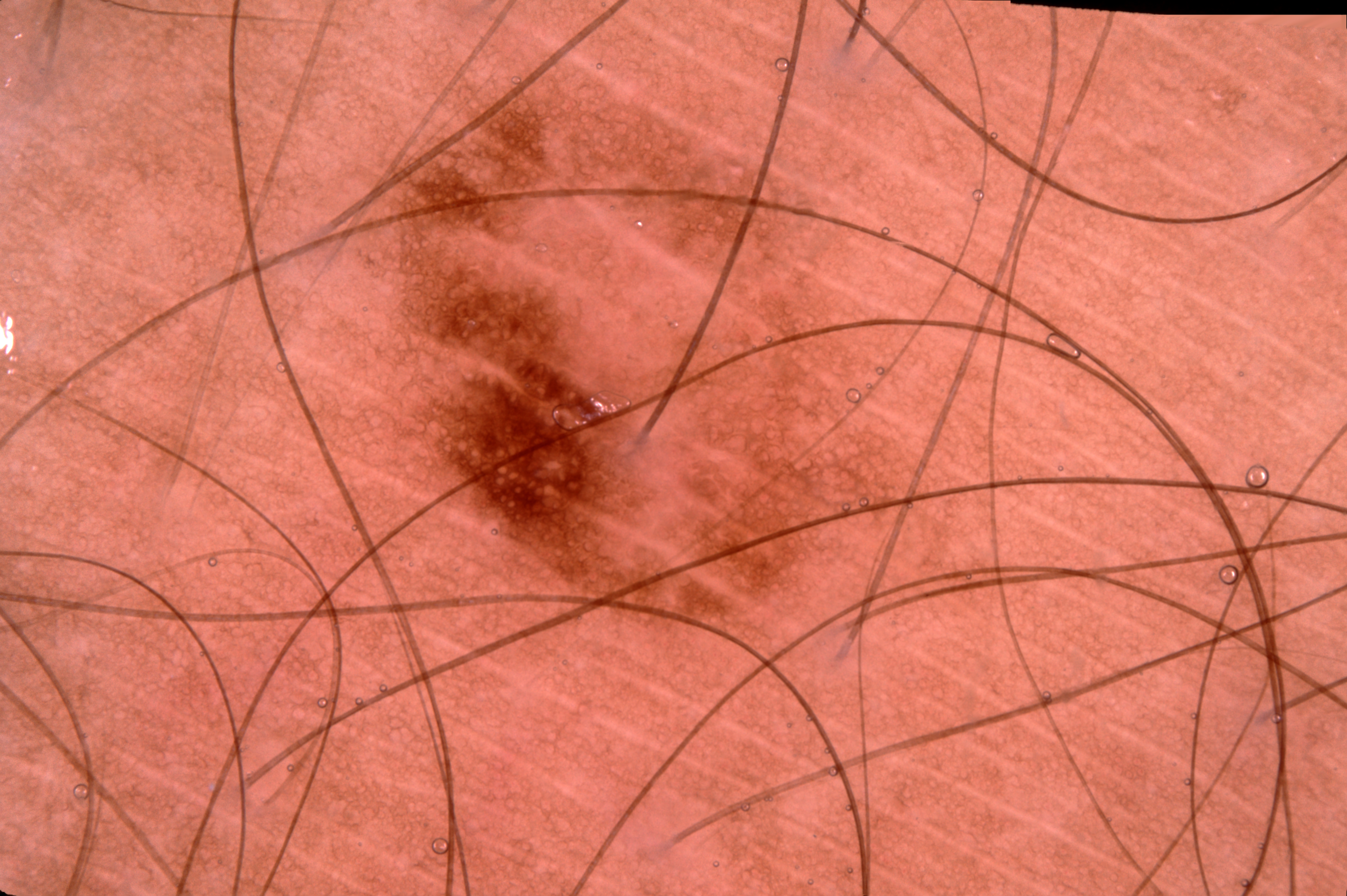Image and clinical context: A dermatoscopic image of a skin lesion. Dermoscopic examination shows pigment network; no milia-like cysts, streaks, or negative network. The lesion occupies roughly 20% of the field. The lesion occupies the region left=376, top=47, right=941, bottom=653. Impression: The lesion was assessed as a melanocytic nevus, a benign lesion.